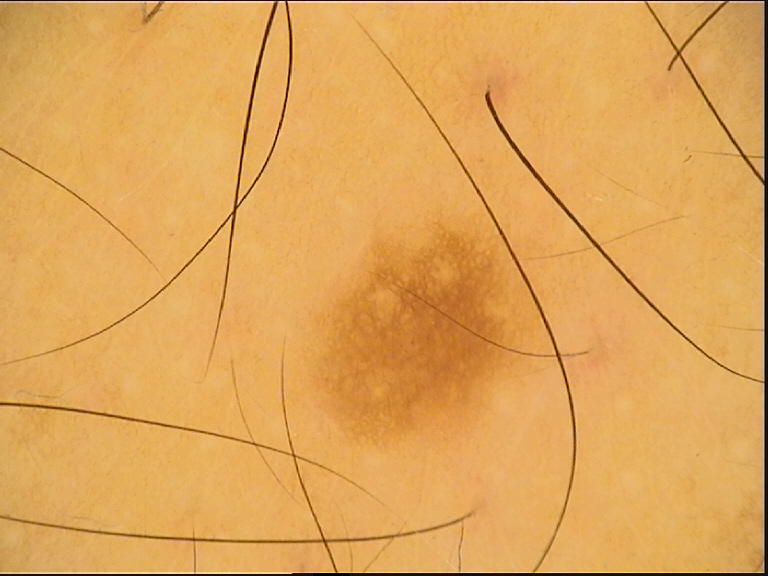Classified as a dysplastic junctional nevus.